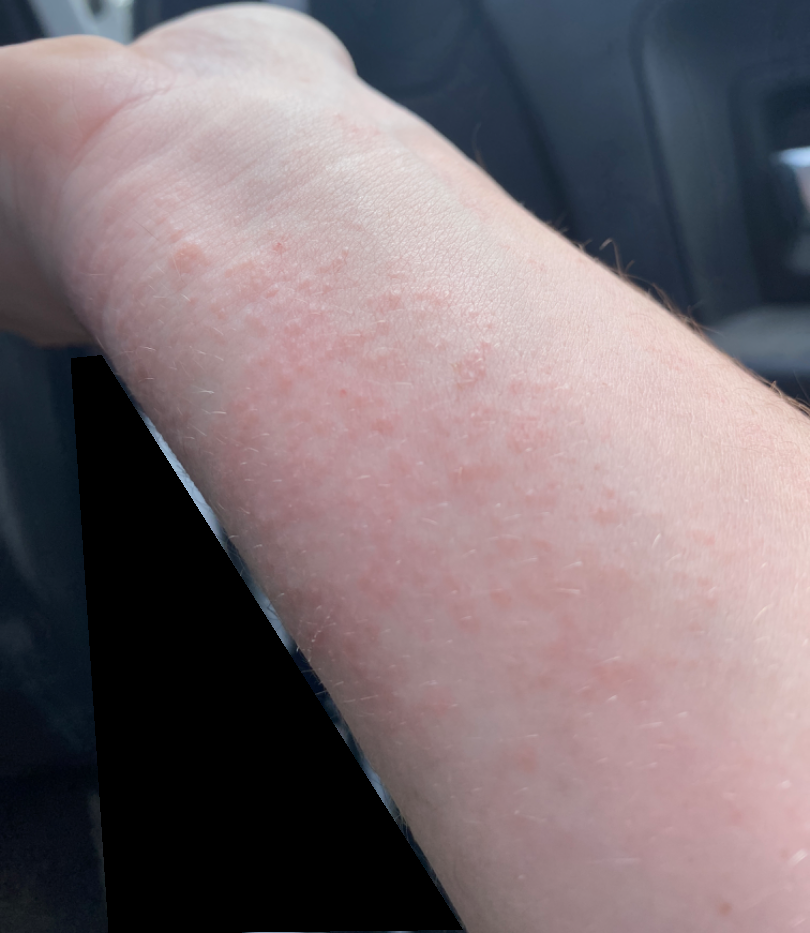Reported duration is less than one week.
An image taken at an angle.
The patient described the issue as a rash.
Reported lesion symptoms include itching and bothersome appearance.
The patient reports the lesion is raised or bumpy.
Located on the arm.
FST II; human graders estimated a MST of 2.
On photographic review: Acute dermatitis, NOS (favored).